Texture is reported as rough or flaky. The affected area is the leg. Present for one to three months. FST IV. The contributor reports itching. This image was taken at an angle — 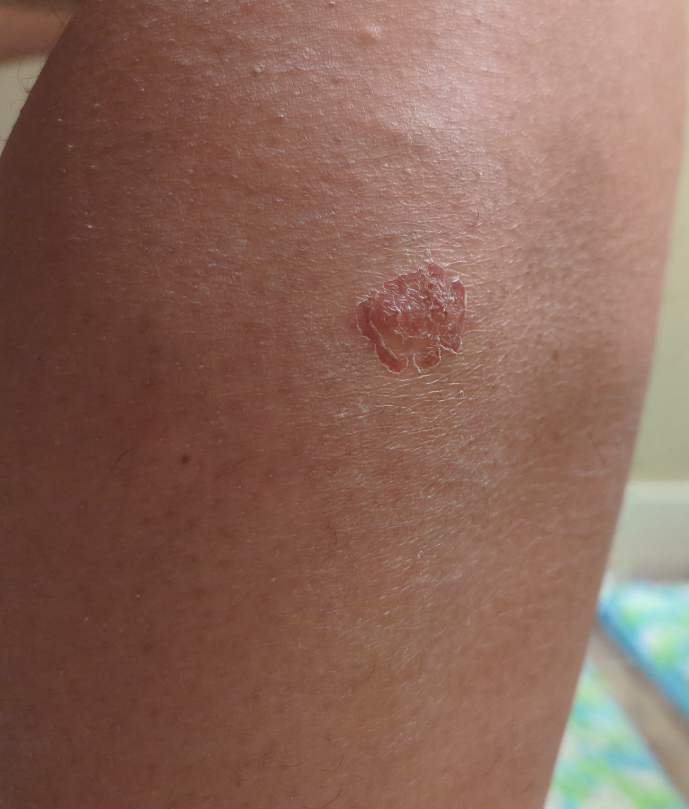Q: Could the case be diagnosed?
A: unable to determine